This is a close-up image: 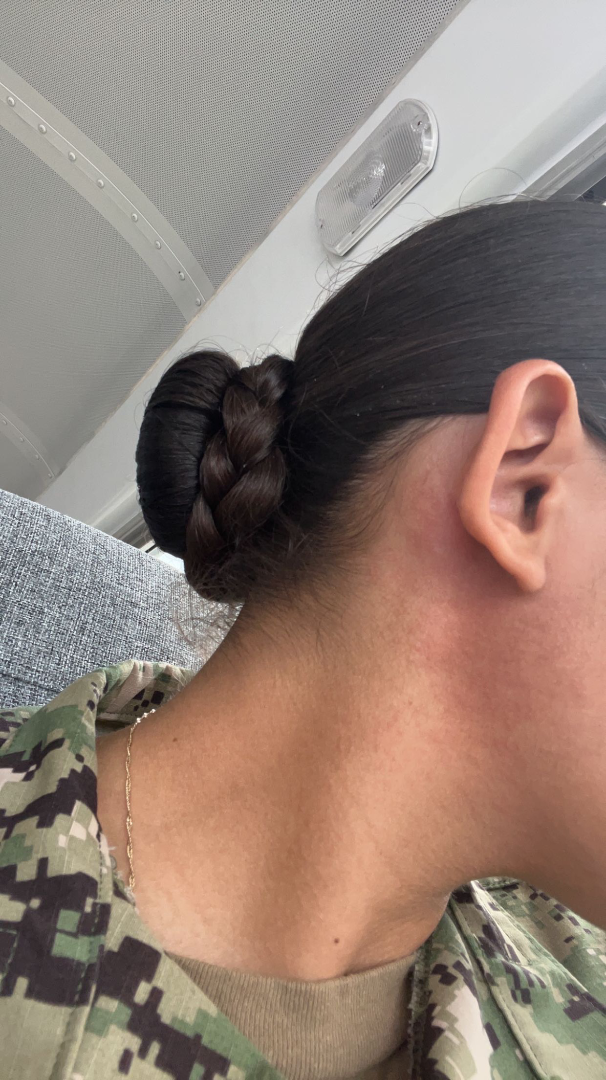The reviewing dermatologist's impression was: Allergic Contact Dermatitis (weight 0.55); Eczema (weight 0.27); Seborrheic Dermatitis (weight 0.18).